This is a dermoscopic photograph of a skin lesion · a male patient, aged around 75:
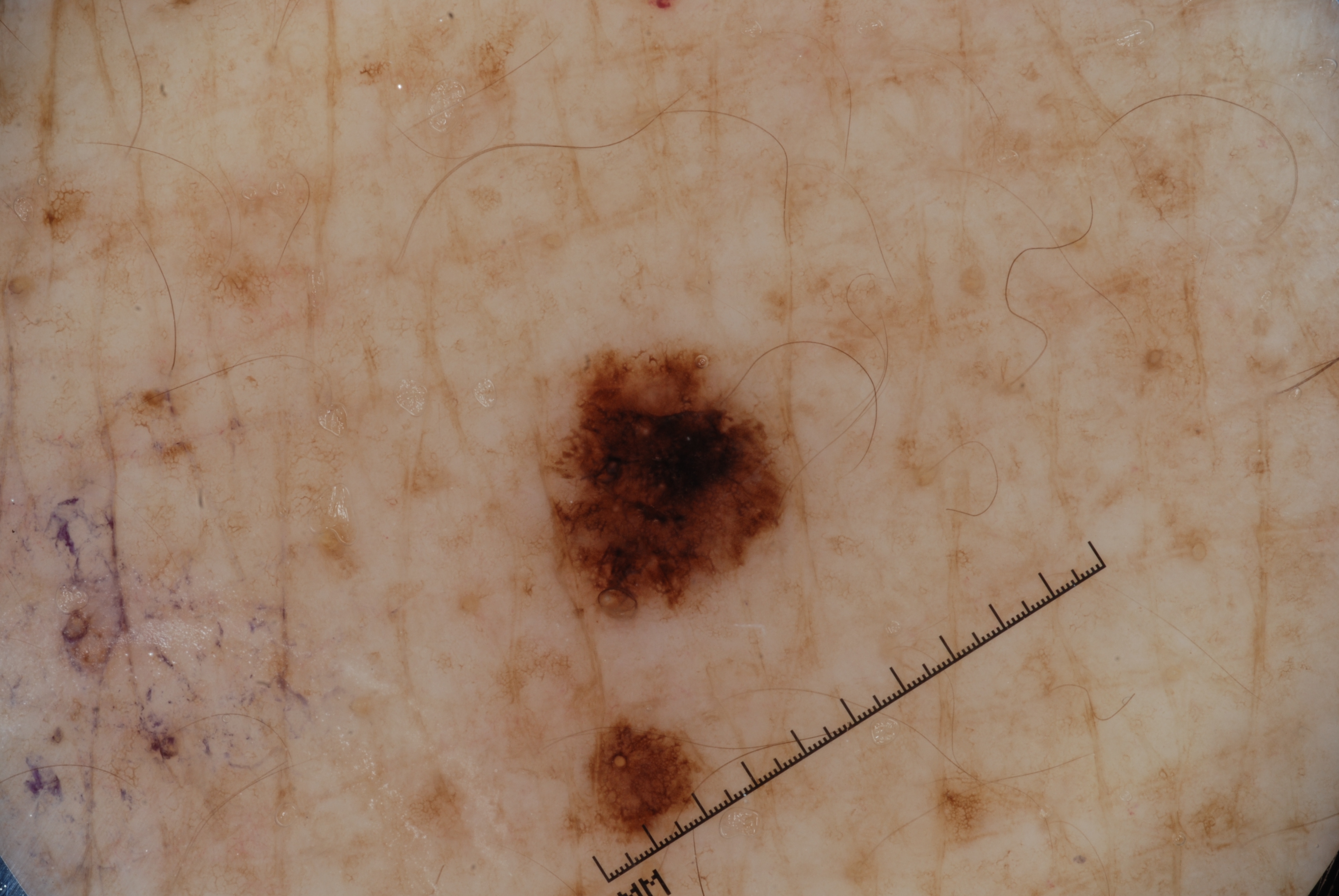The lesion covers approximately 4% of the dermoscopic field. On dermoscopy, the lesion shows pigment network and milia-like cysts, with no negative network or streaks. Lesion location: <box>544, 350, 795, 609</box>. Consistent with a melanocytic nevus, a benign lesion.